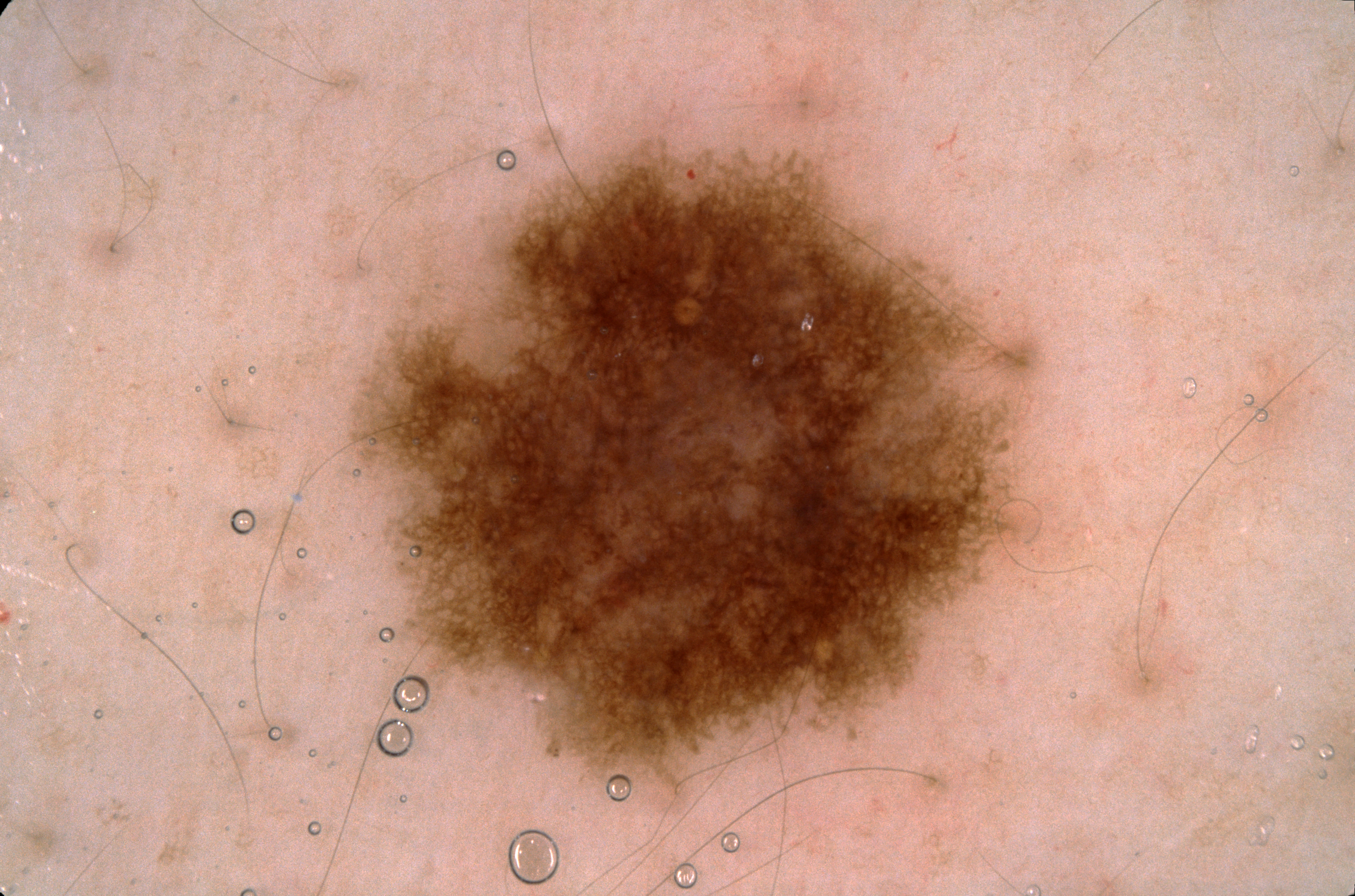A male subject, aged approximately 35. A dermoscopic close-up of a skin lesion. The lesion takes up a moderate portion of the field. With coordinates (x1, y1, x2, y2), the lesion occupies the region 348, 135, 1038, 802. Dermoscopy demonstrates pigment network; no streaks, milia-like cysts, or negative network. The lesion was assessed as a melanocytic nevus, a benign lesion.